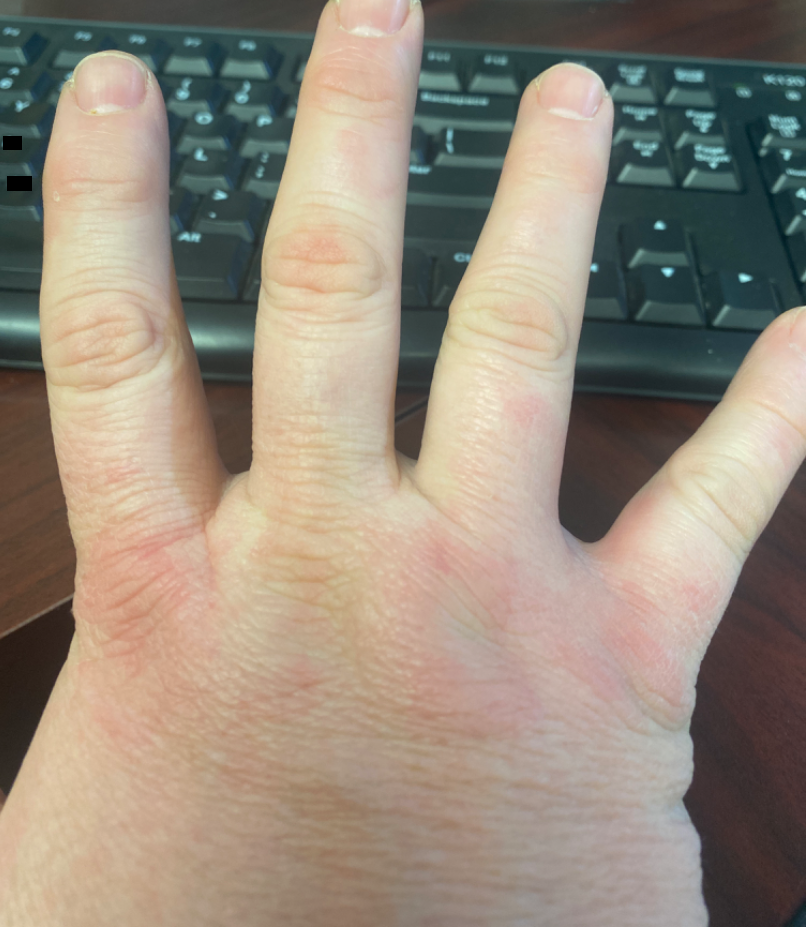The back of the hand and palm are involved.
Texture is reported as raised or bumpy.
The patient also reports joint pain and fatigue.
The condition has been present for less than one week.
A close-up photograph.
The patient is a male aged 40–49.
The patient described the issue as a rash.
Eczema and Granuloma annulare were considered with similar weight; a remote consideration is Urticaria; less likely is Allergic Contact Dermatitis; less probable is Irritant Contact Dermatitis.